The contributor notes the lesion is raised or bumpy. The patient considered this a rash. Close-up view. The affected area is the head or neck. Reported lesion symptoms include enlargement, itching, burning and pain. The patient is a female aged 50–59 — 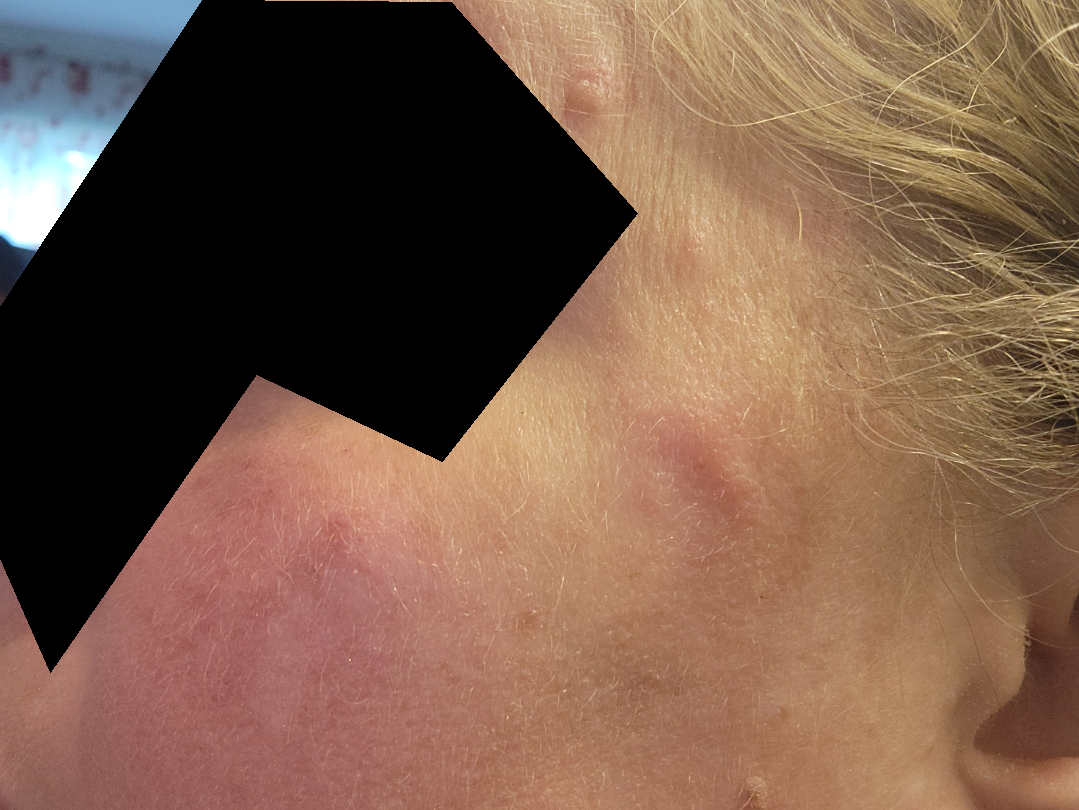differential — Rosacea, Allergic Contact Dermatitis and Cutaneous lupus were considered with similar weight